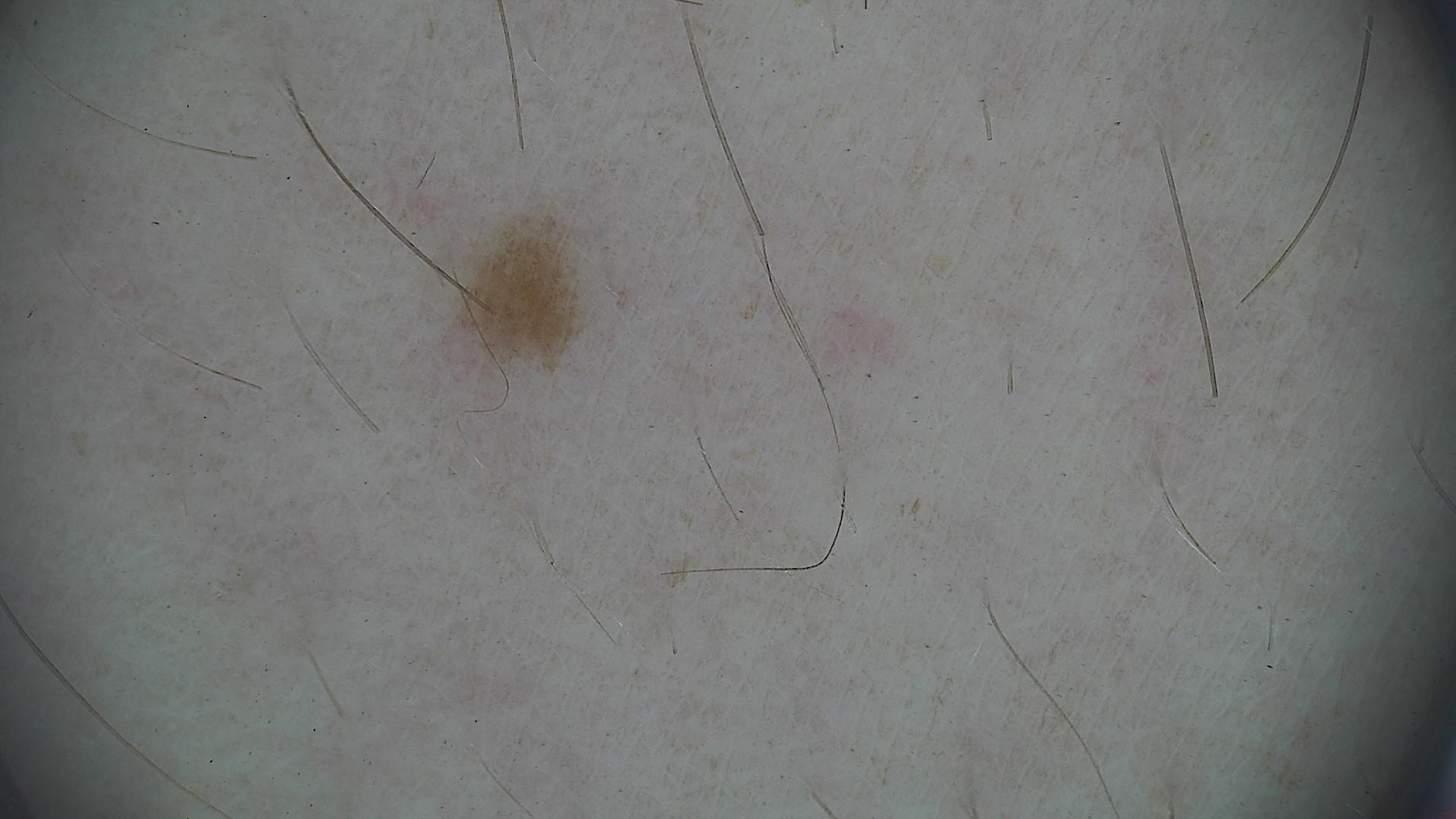The diagnostic label was a banal lesion — a junctional nevus.